The subject is a female aged 30–39. The photograph is a close-up of the affected area. The lesion is described as raised or bumpy and rough or flaky. Located on the back of the hand. The patient indicates the condition has been present for one to four weeks. Reported lesion symptoms include burning, itching and bothersome appearance: 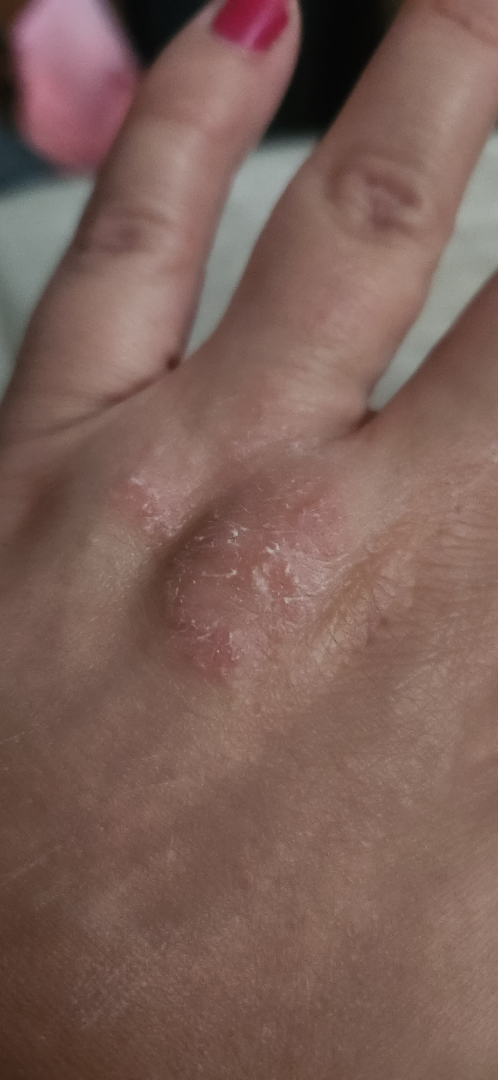The impression is Chronic dermatitis, NOS.